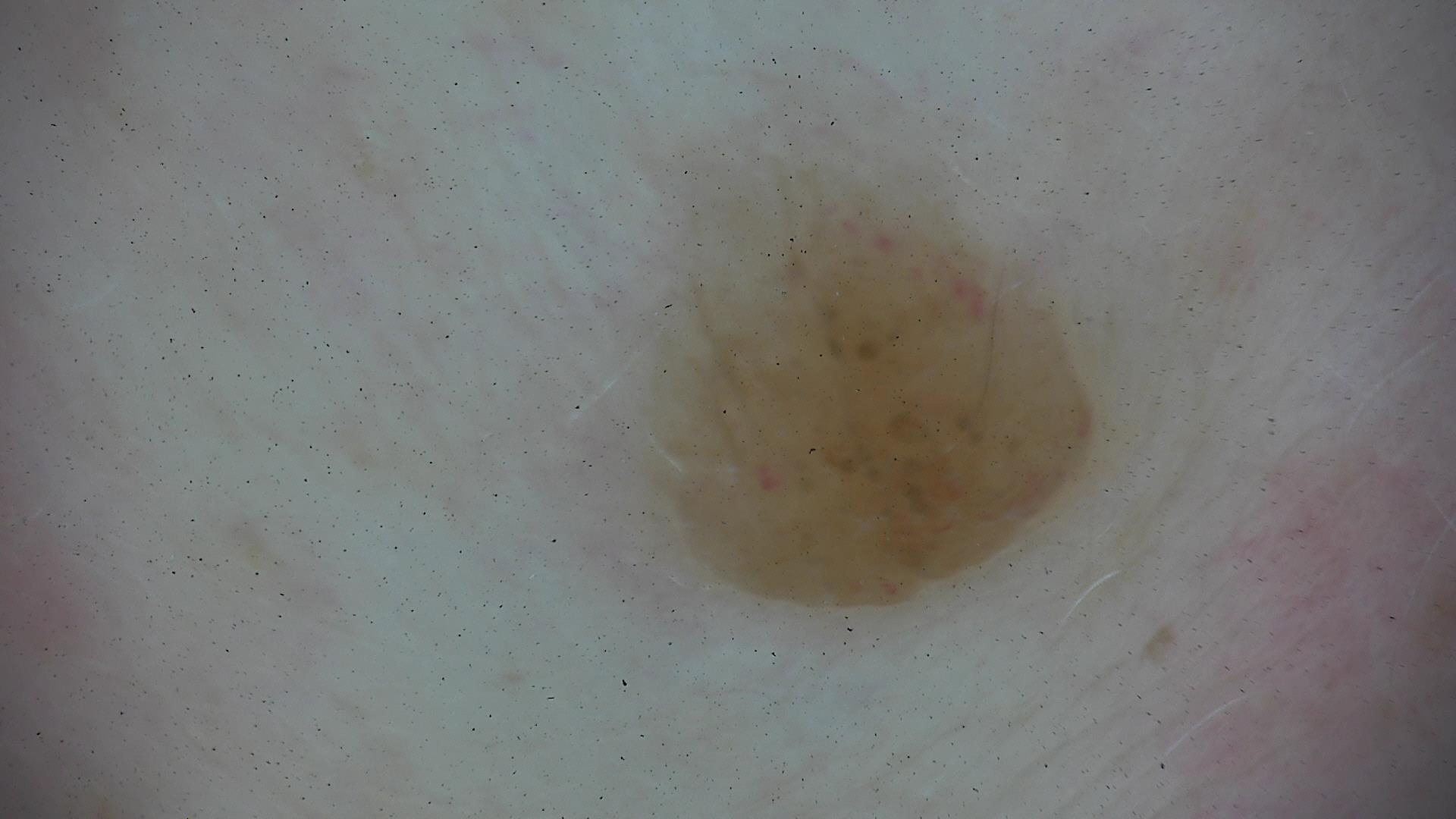Conclusion: The diagnostic label was a banal lesion — a dermal nevus.